A female subject aged 73-77 · a clinical photograph showing a skin lesion in context · skin type II — 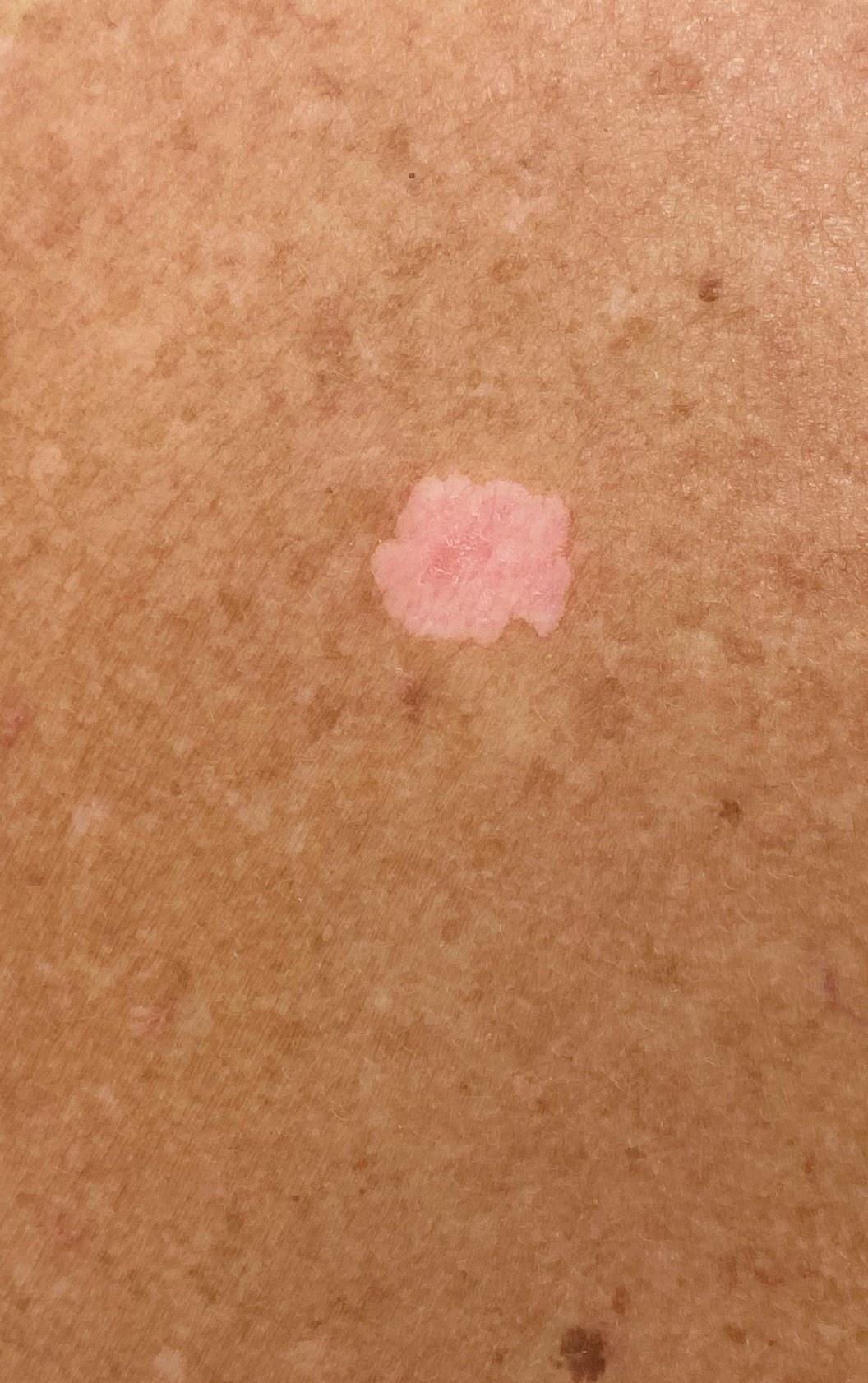body site: the posterior trunk; diagnosis: Solar or actinic keratosis (biopsy-proven).